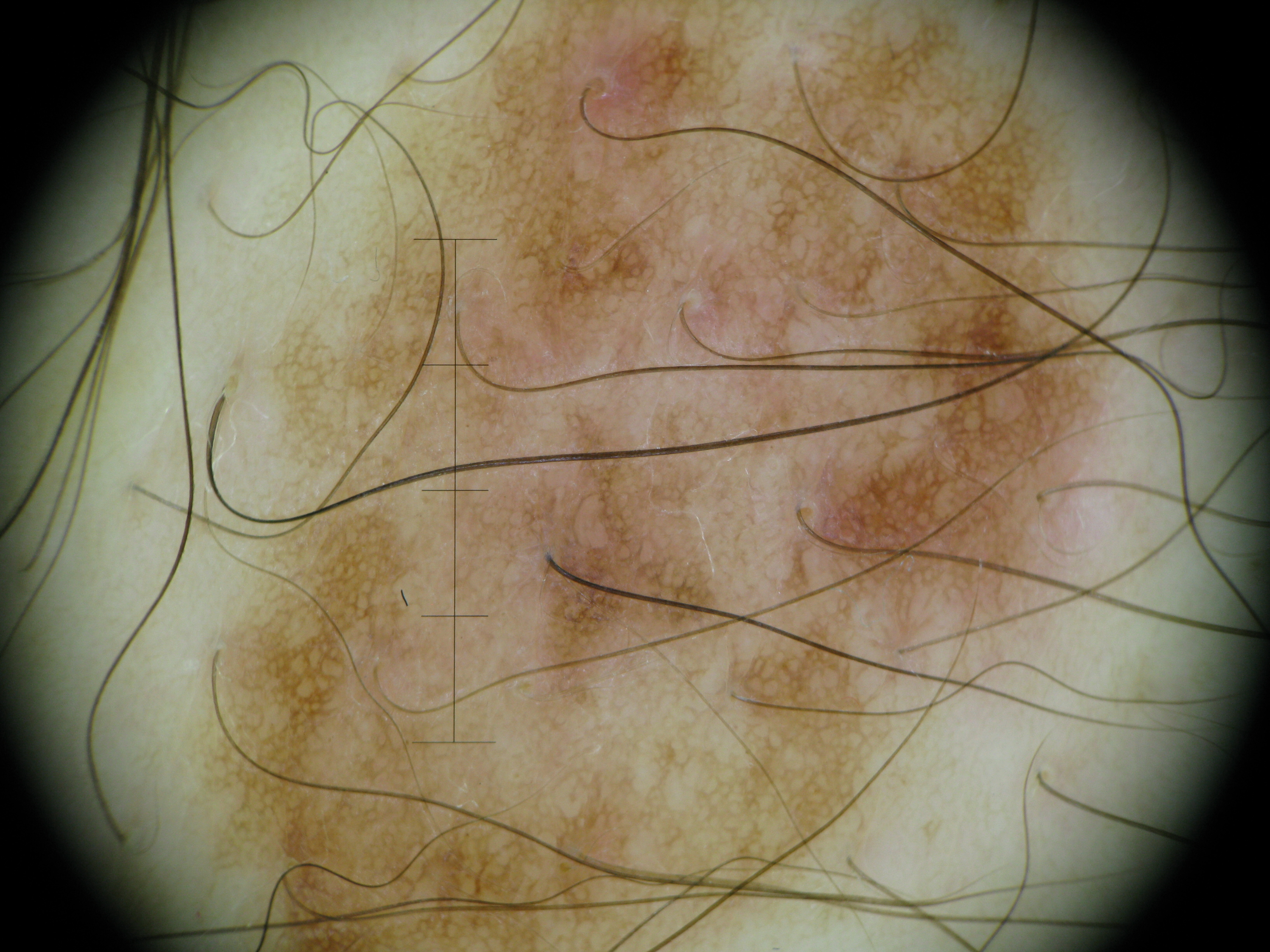Diagnosed as a dysplastic junctional nevus.